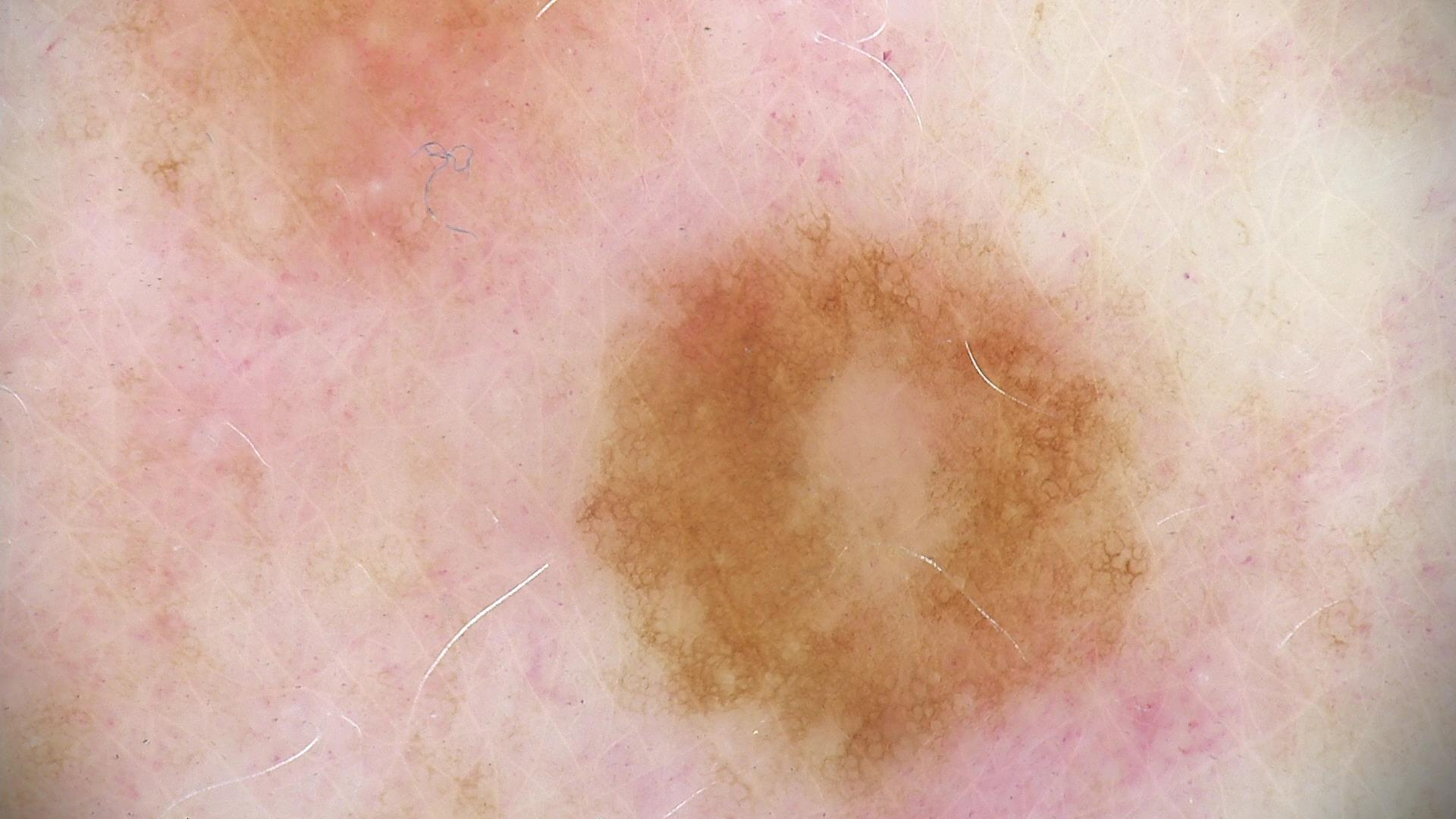Consistent with a dysplastic junctional nevus.